The subject is male · the photo was captured at a distance:
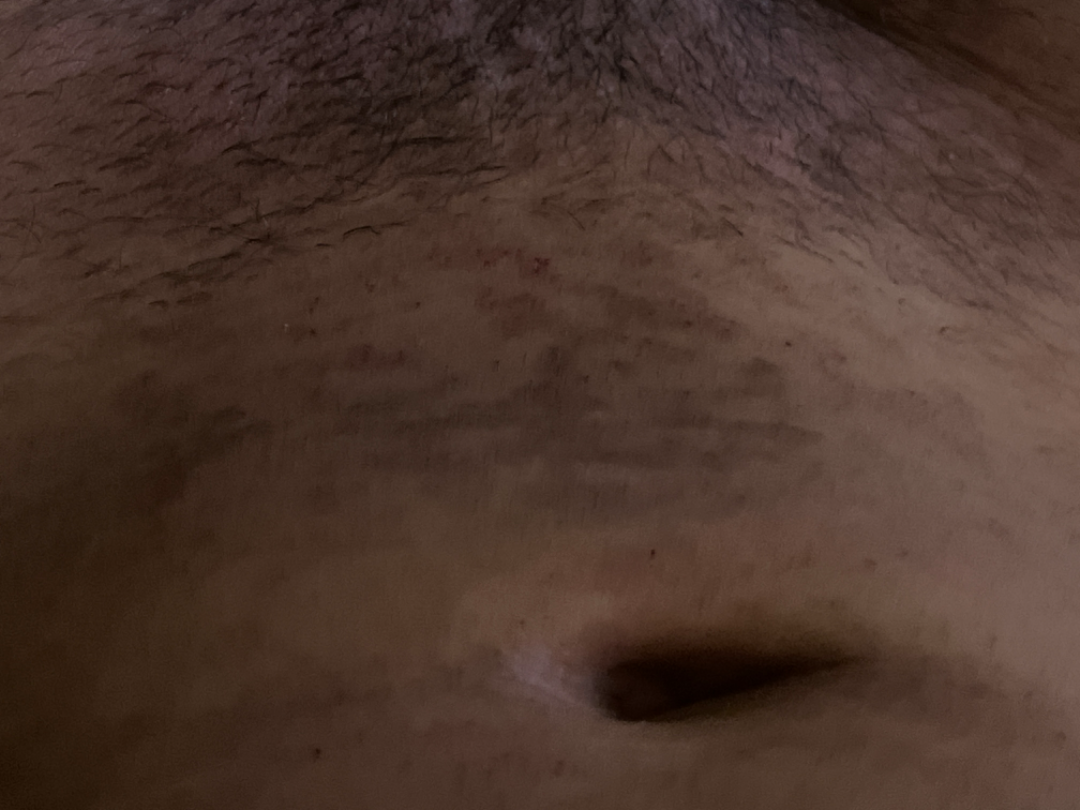Case summary:
- clinical impression: the favored diagnosis is Confluent and reticulate papillomatosis; also consider Tinea Versicolor; an alternative is Post-Inflammatory hyperpigmentation